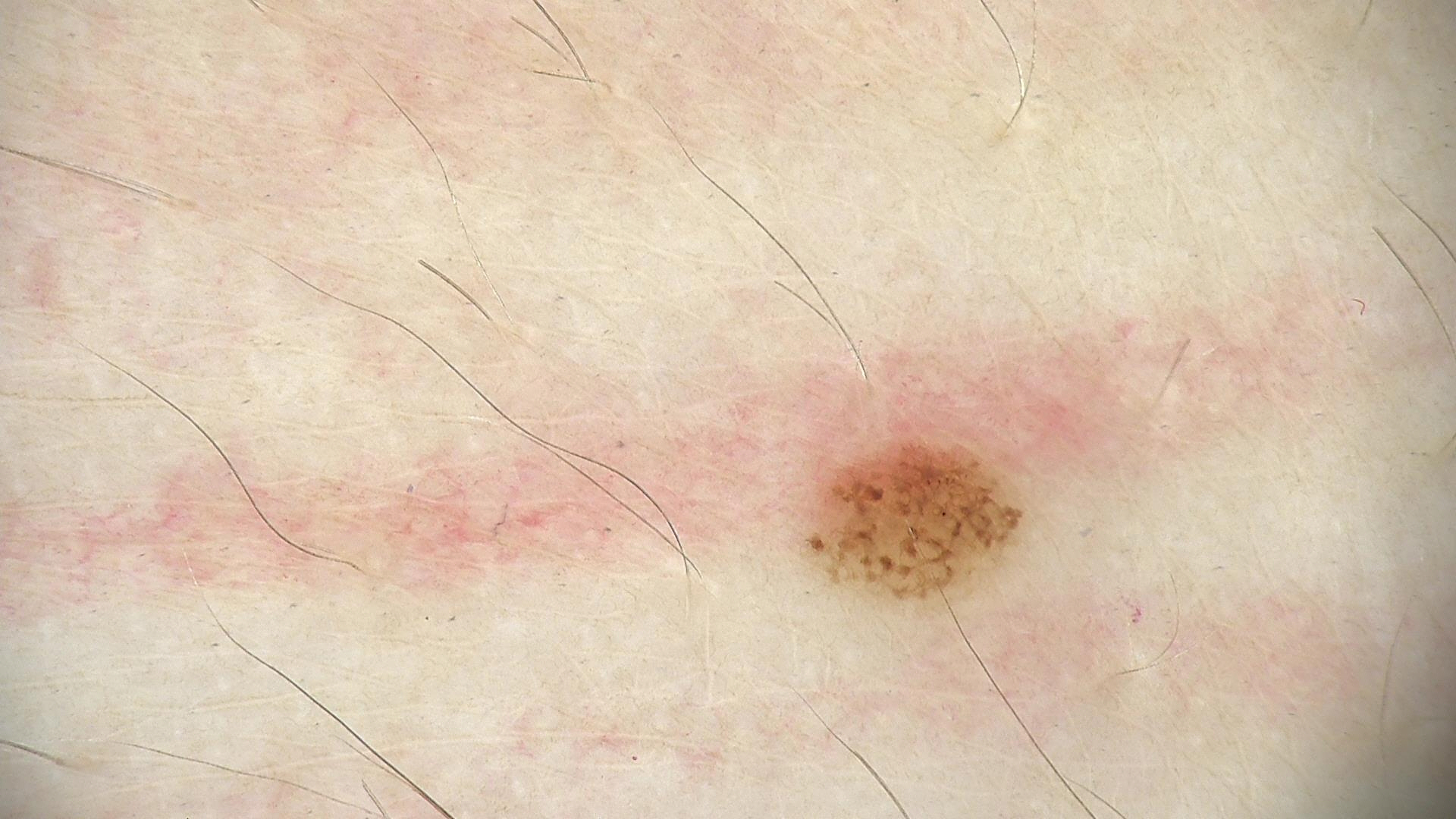| key | value |
|---|---|
| image type | dermoscopy |
| label | dysplastic junctional nevus (expert consensus) |